The photo was captured at a distance · the lesion involves the front of the torso and head or neck: 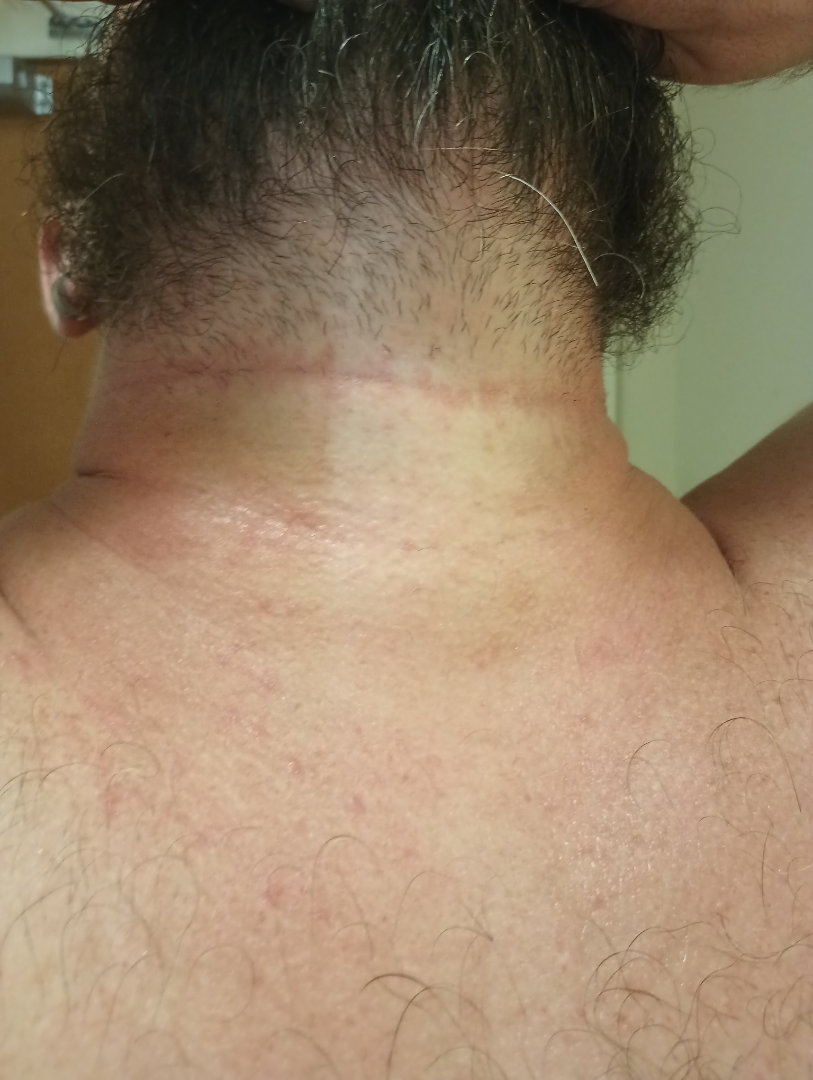assessment=ungradable on photographic review
symptoms=burning, itching, pain and bothersome appearance
lesion texture=raised or bumpy and rough or flaky
present for=less than one week